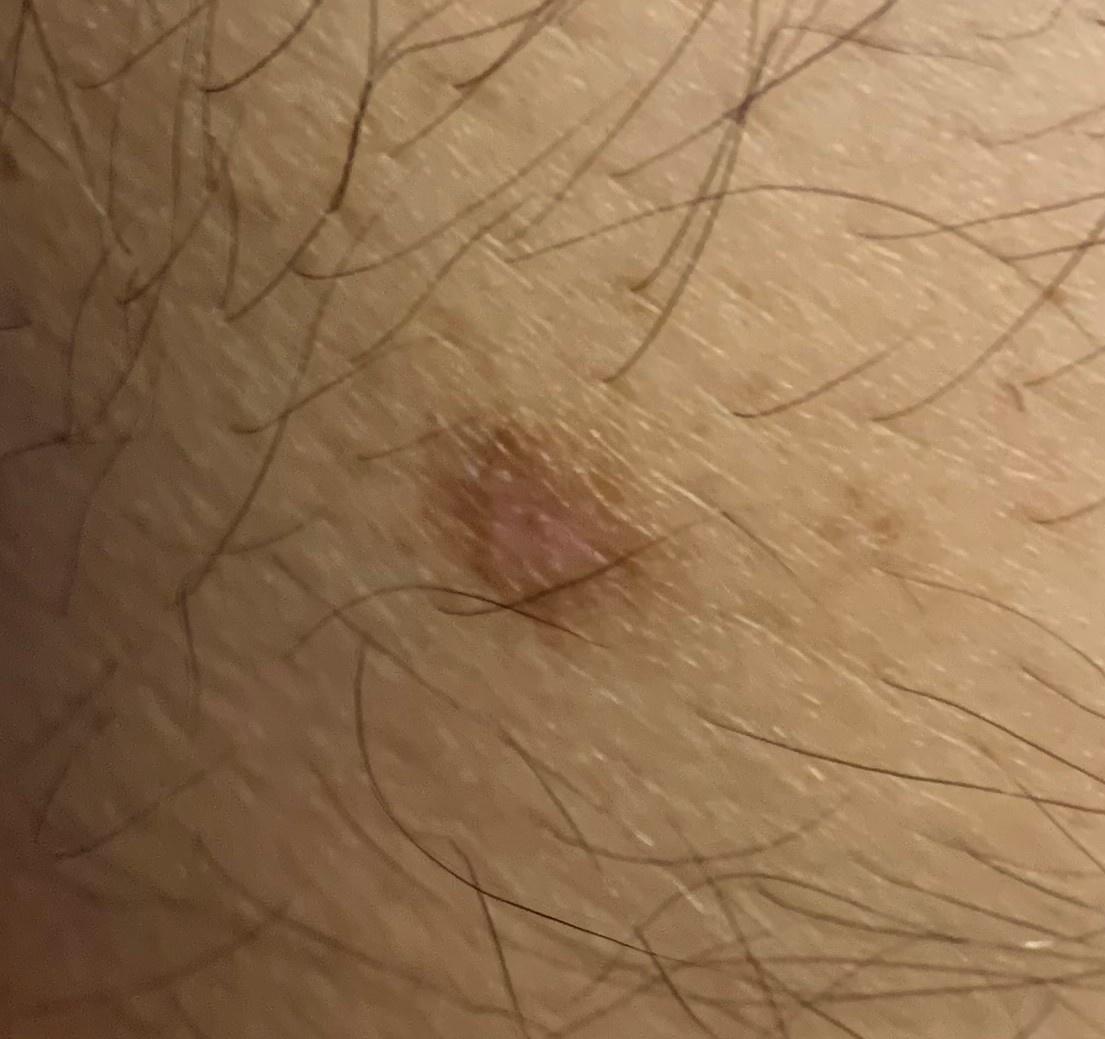A clinical overview photograph of a skin lesion. A male patient aged around 45. The lesion was found on a lower extremity. Clinically diagnosed as a dermatofibroma.